The photograph was taken at an angle · FST II; human graders estimated Monk skin tone scale 3.
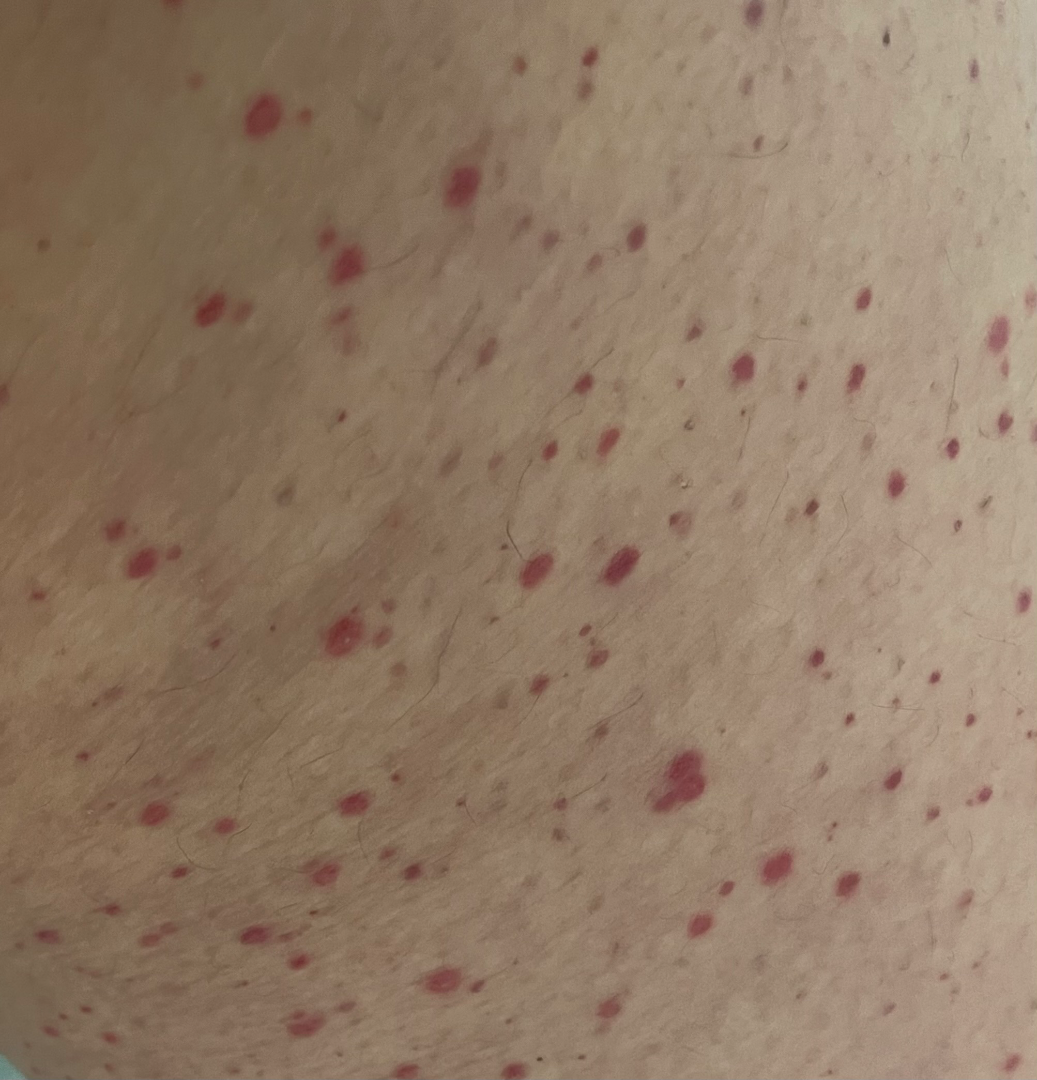Findings:
– differential — the impression was split between Purpura and Vasculitis of the skin